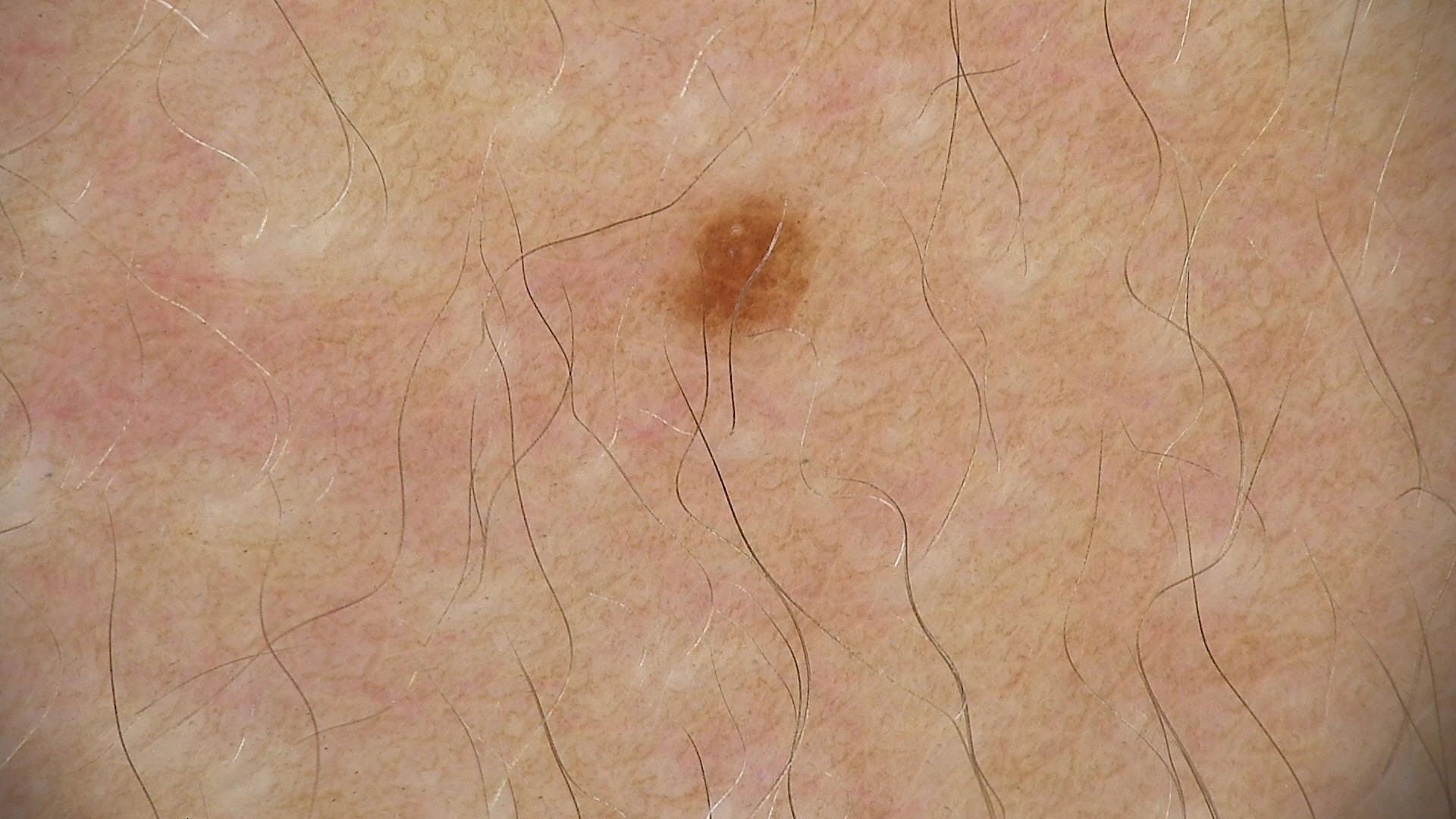Conclusion: Labeled as a dysplastic junctional nevus.